The patient says their skin tans without first burning. A macroscopic clinical photograph of a skin lesion. The patient reports a personal history of cancer and a family history of skin cancer. A female subject 92 years old:
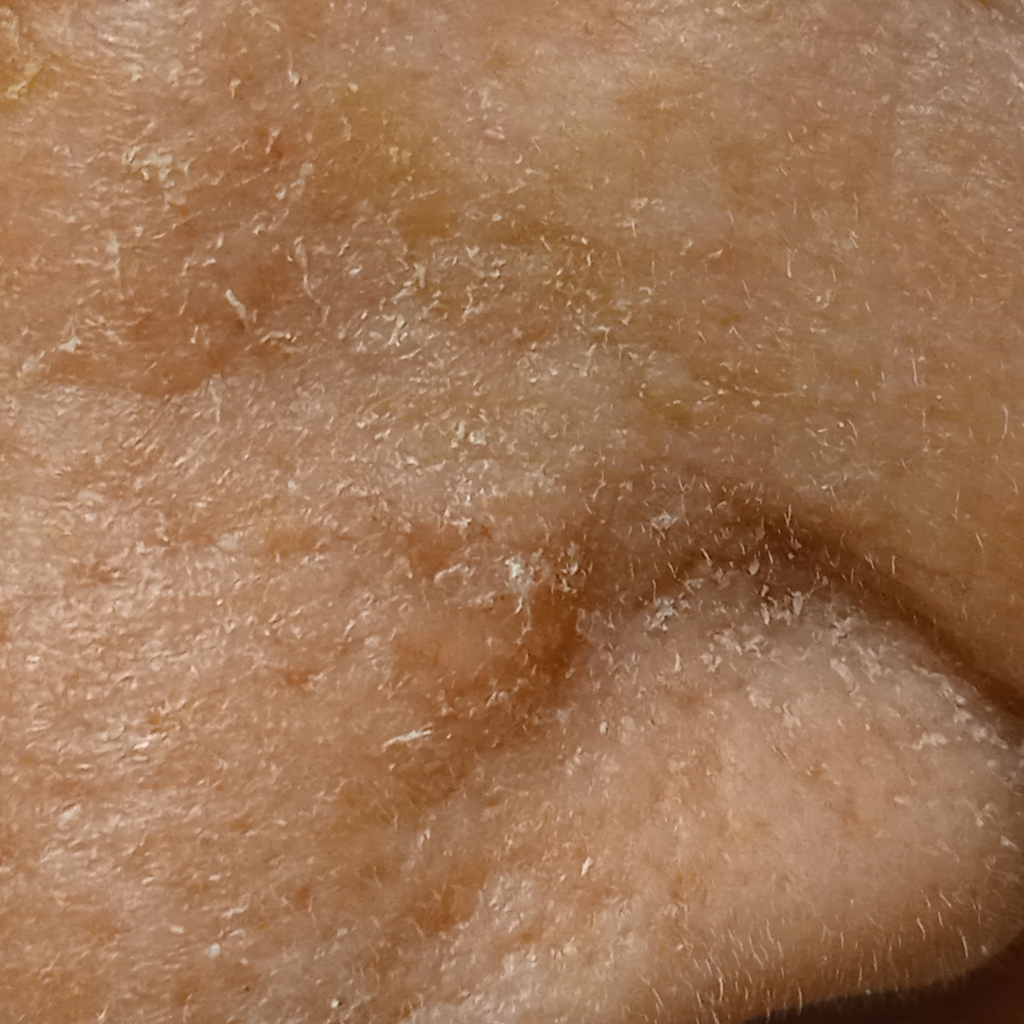Q: What is the anatomic site?
A: the face
Q: Lesion size?
A: 7 mm
Q: What was the diagnosis?
A: basal cell carcinoma (dermatologist consensus)